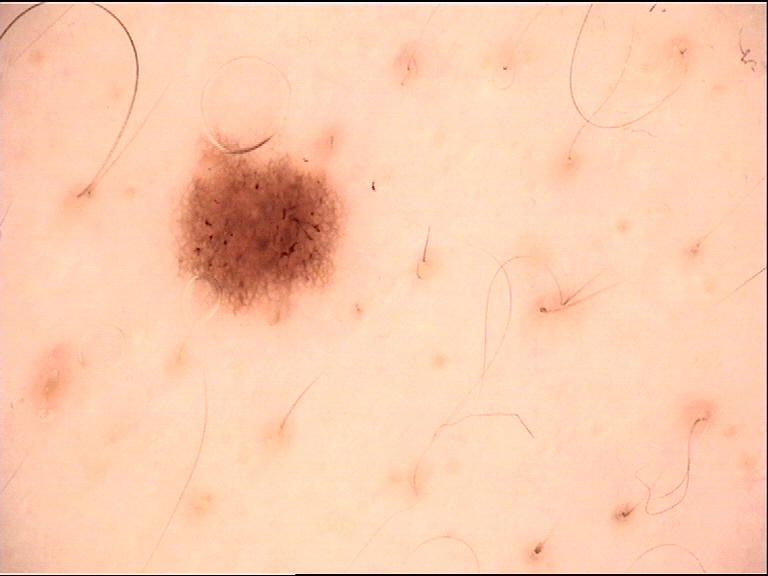| feature | finding |
|---|---|
| image type | dermatoscopy |
| label | dysplastic junctional nevus (expert consensus) |